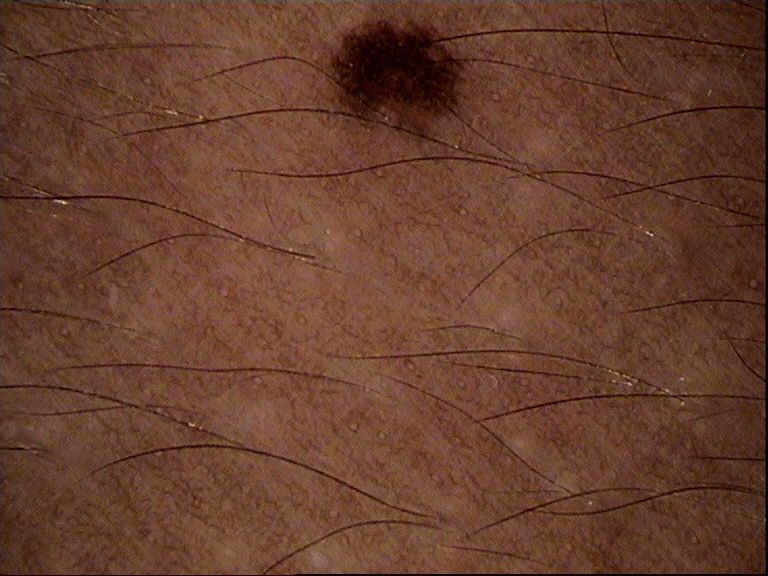Conclusion: Diagnosed as a banal lesion — a junctional nevus.